A dermoscopic view of a skin lesion. A male subject, approximately 40 years of age — 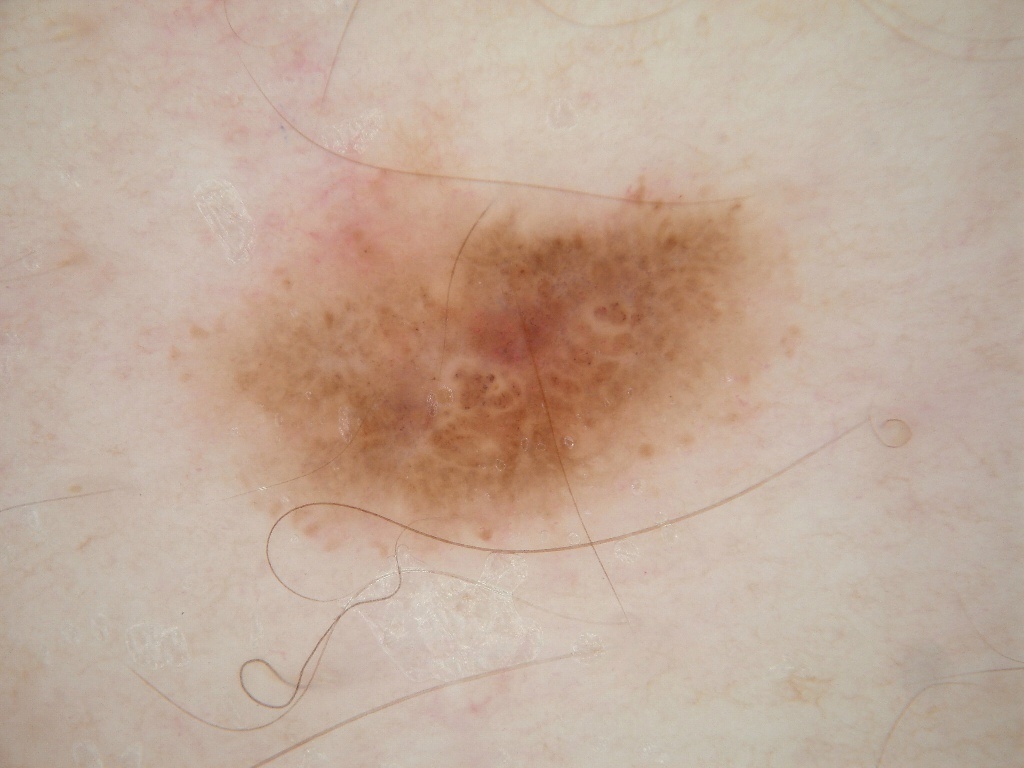dermoscopic findings = streaks, globules, and negative network; absent: pigment network and milia-like cysts | location = bbox=[138, 108, 835, 572] | extent = large | impression = a melanoma.